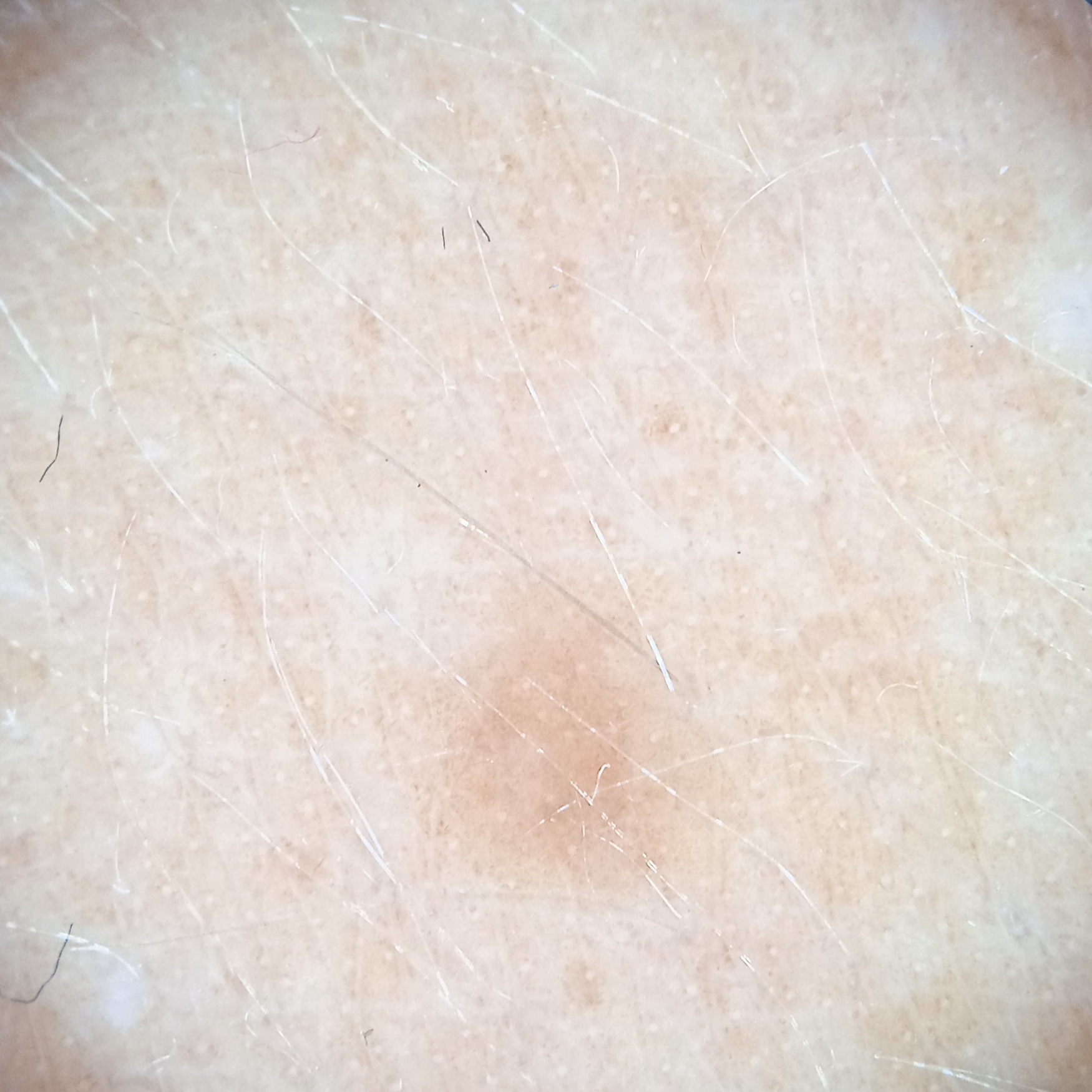The lesion was left diagnostically undetermined on review. referral context = research study (no referral diagnosis)
sun reaction = skin tans without first burning
risk factors = a history of sunbed use
nevus count = a moderate number of melanocytic nevi
patient = female, 47 years old
modality = dermoscopic image
anatomic site = the back
lesion size = 3.5 mm